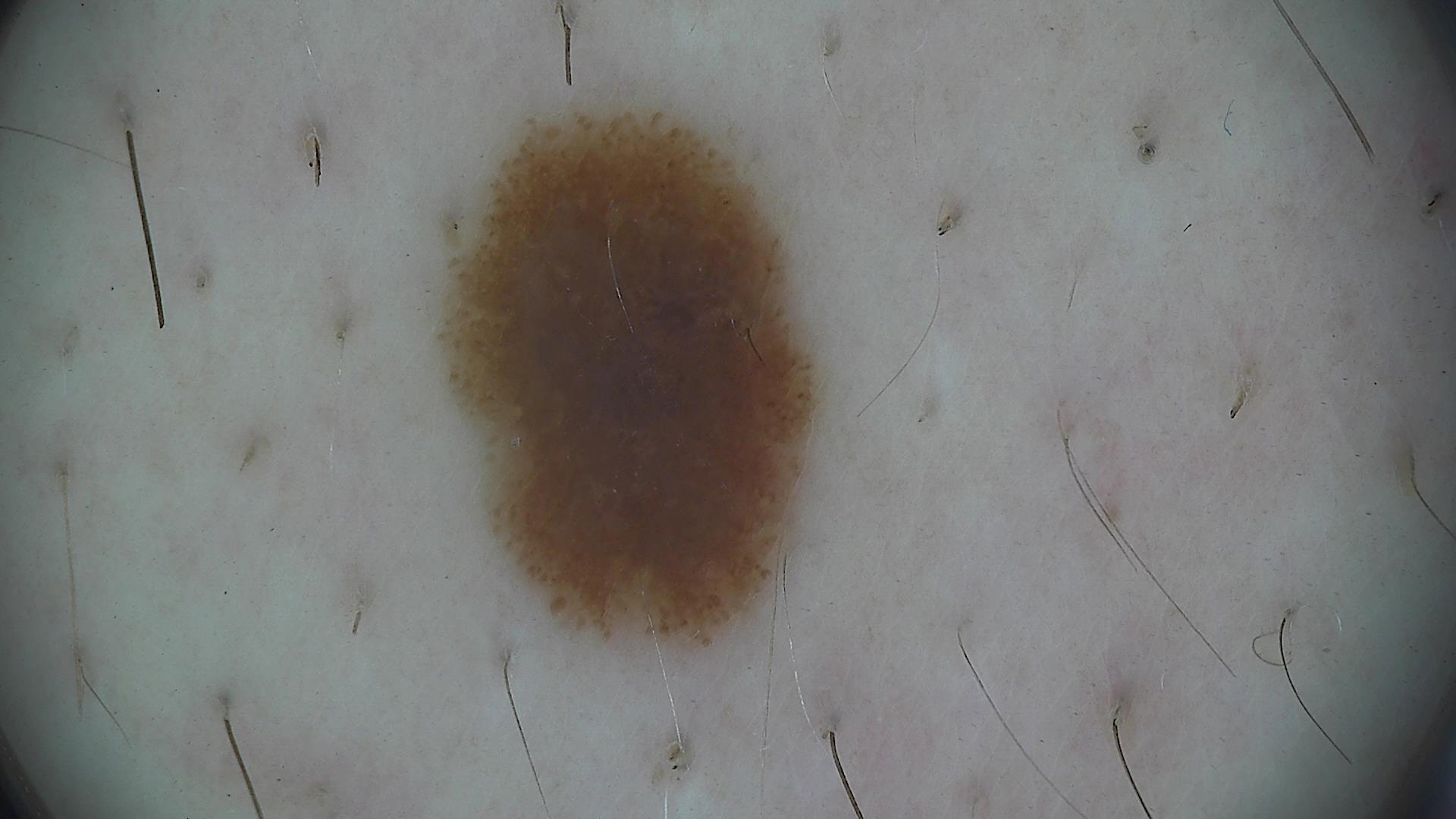{
  "image": "dermatoscopy",
  "diagnosis": {
    "name": "dysplastic junctional nevus",
    "code": "jd",
    "malignancy": "benign",
    "super_class": "melanocytic",
    "confirmation": "expert consensus"
  }
}